Present for less than one week. This is a close-up image. The lesion is described as raised or bumpy. The lesion involves the back of the hand and leg — 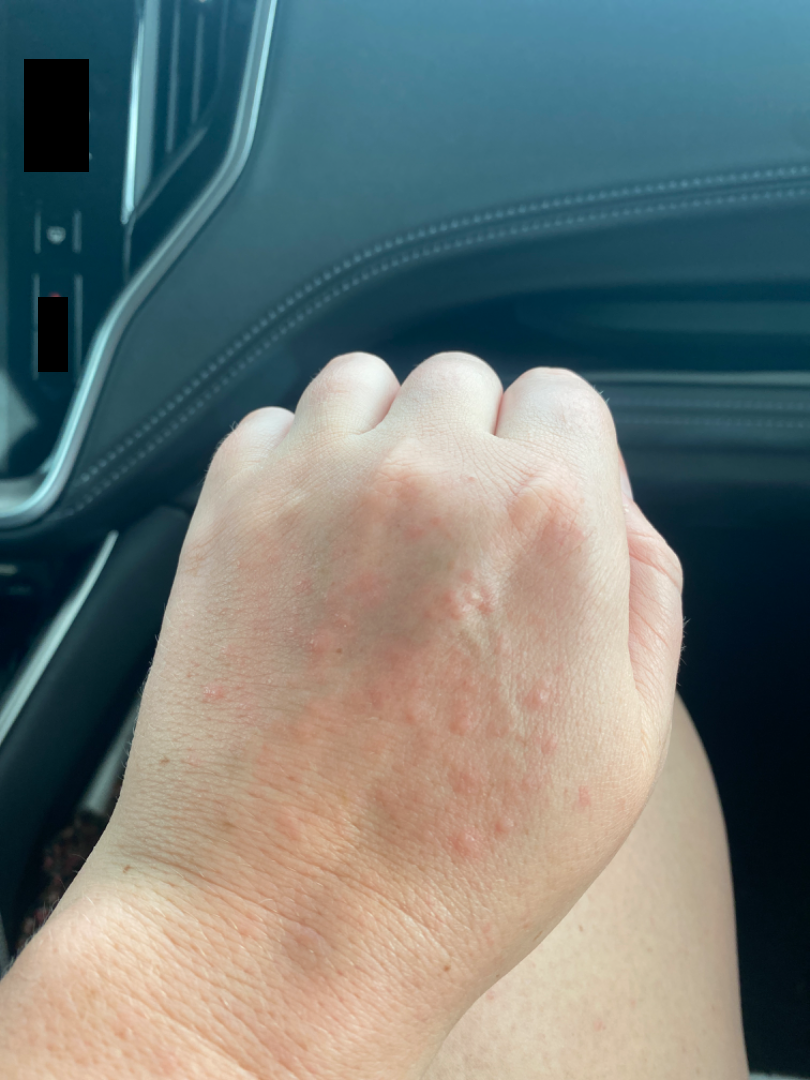Impression: On teledermatology review, most likely Photodermatitis; an alternative is Eczema; a more distant consideration is Cutaneous lupus.